The leg is involved · a close-up photograph.
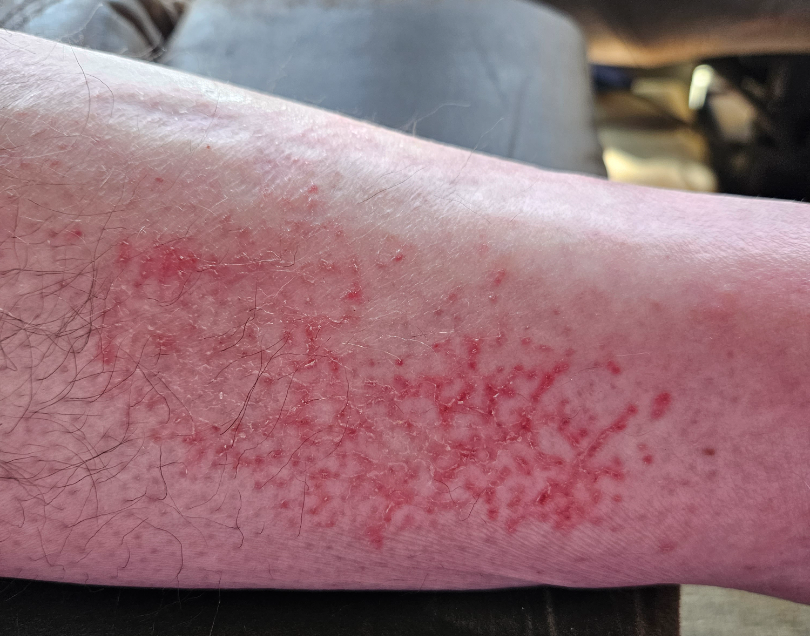  differential: Eczema